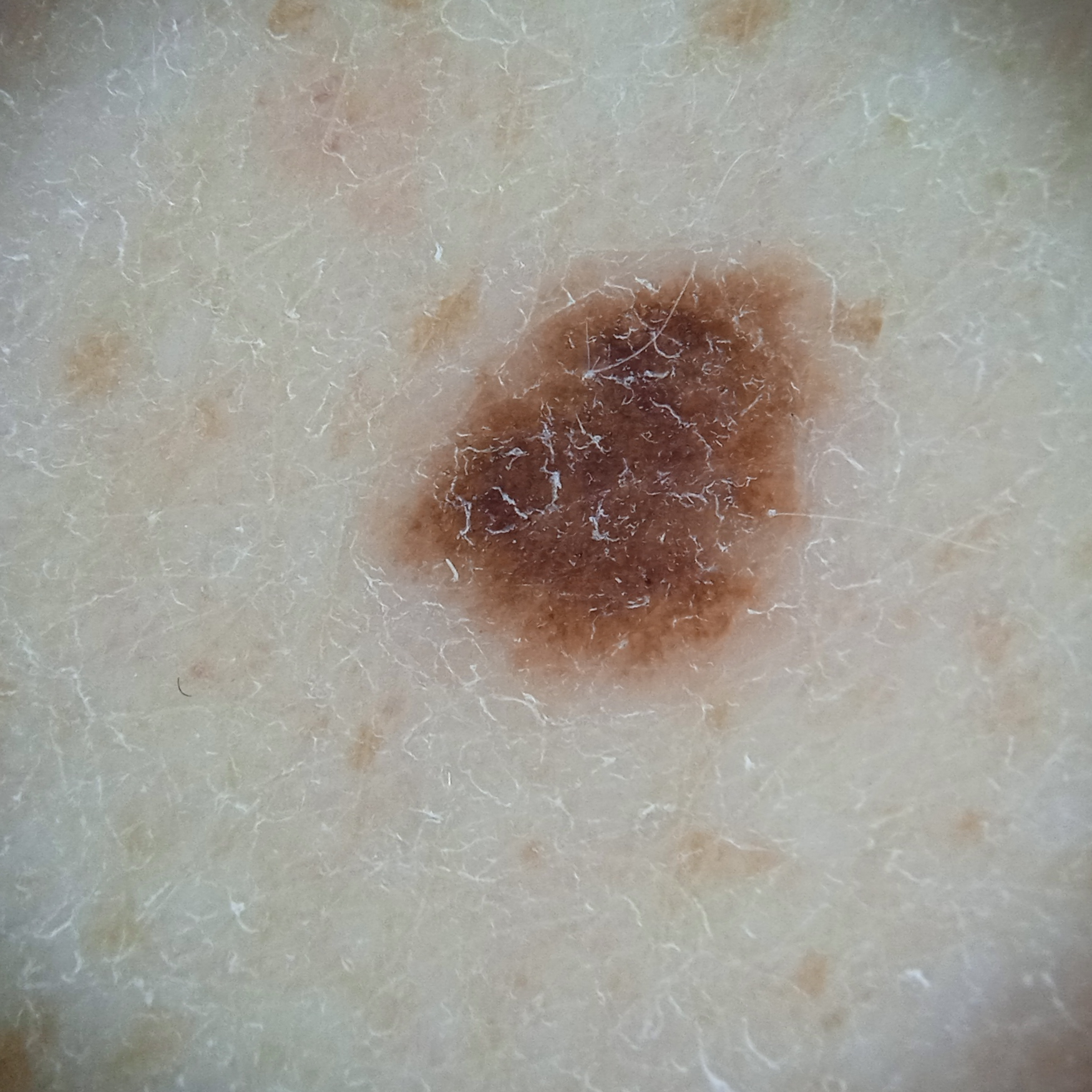{"image": "dermoscopy", "patient": {"age": 72, "sex": "male"}, "lesion_location": "the back", "lesion_size": {"diameter_mm": 5.6}, "diagnosis": {"name": "melanocytic nevus", "malignancy": "benign"}}